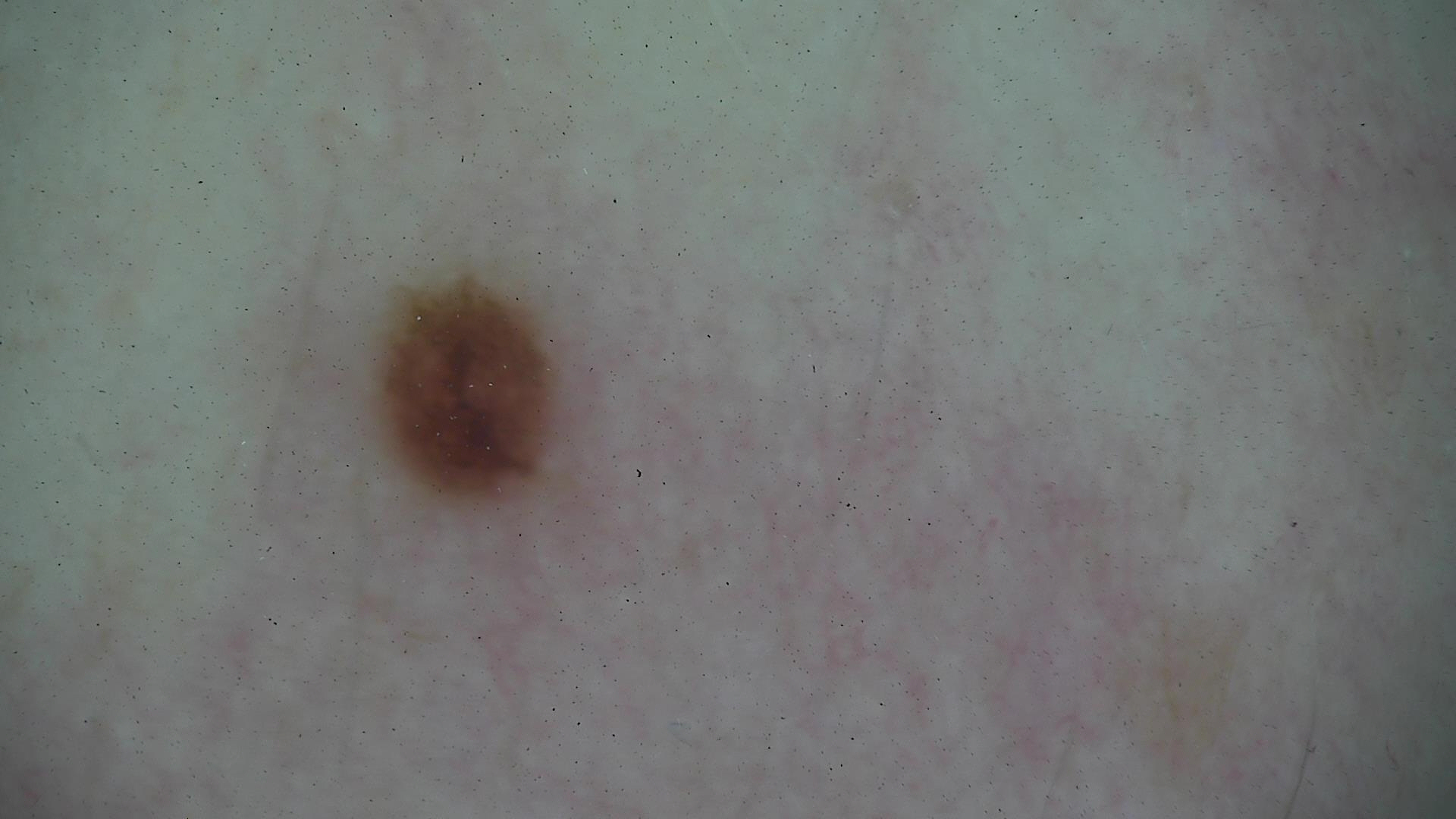class: dysplastic junctional nevus (expert consensus).